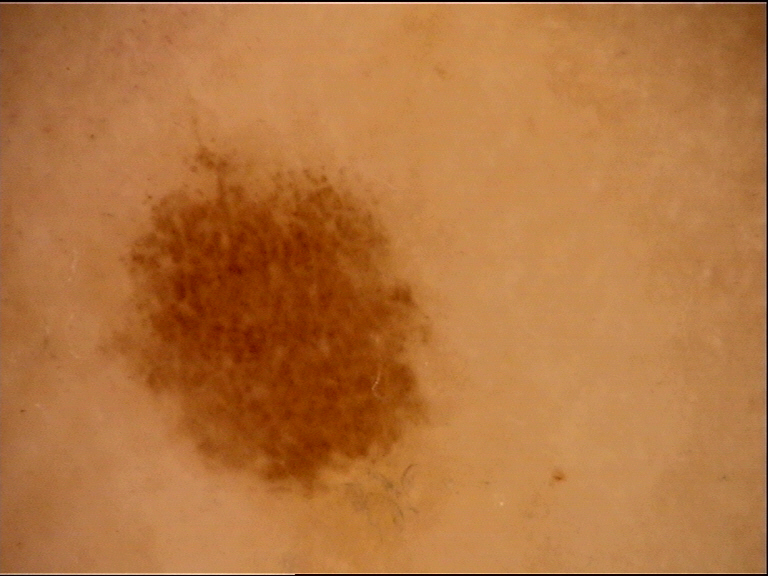Consistent with a benign lesion — a dysplastic junctional nevus.